The lesion involves the leg; this image was taken at an angle; the lesion is described as rough or flaky and raised or bumpy; reported lesion symptoms include itching; skin tone: Fitzpatrick phototype III; the patient reported no systemic symptoms; the condition has been present for one to four weeks; the patient is 18–29, female:
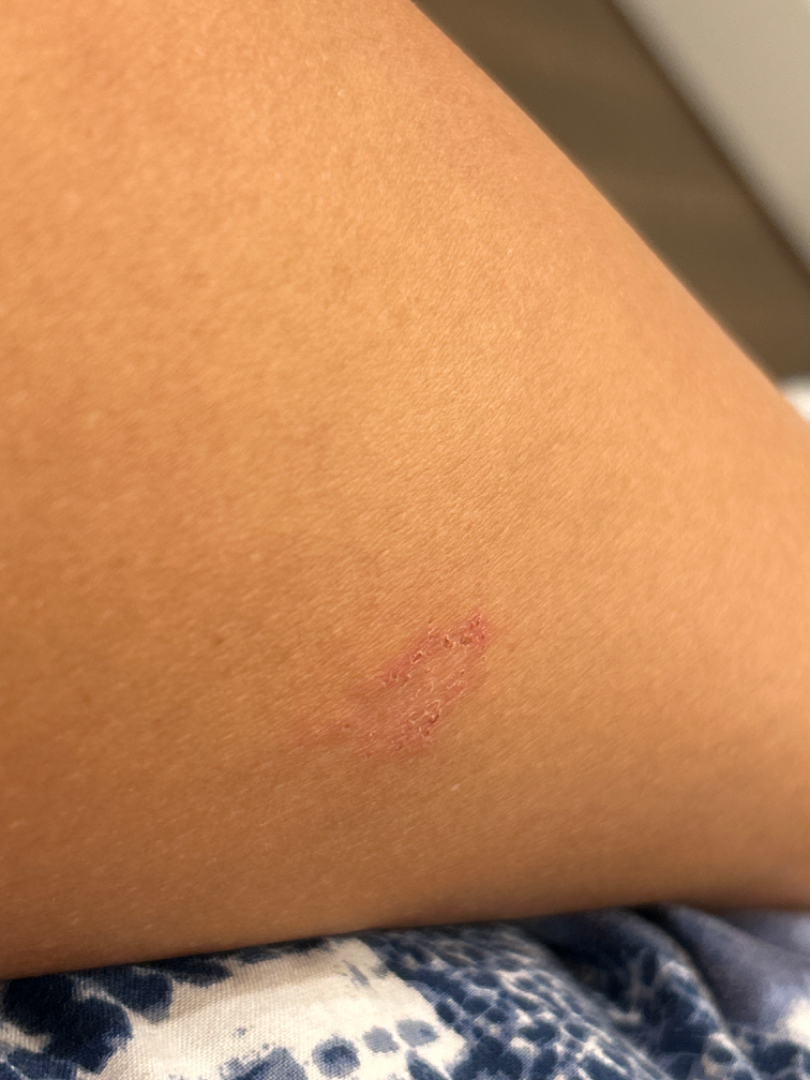The leading impression is Superficial wound of body region; the differential also includes Tinea; also consider Eczema.